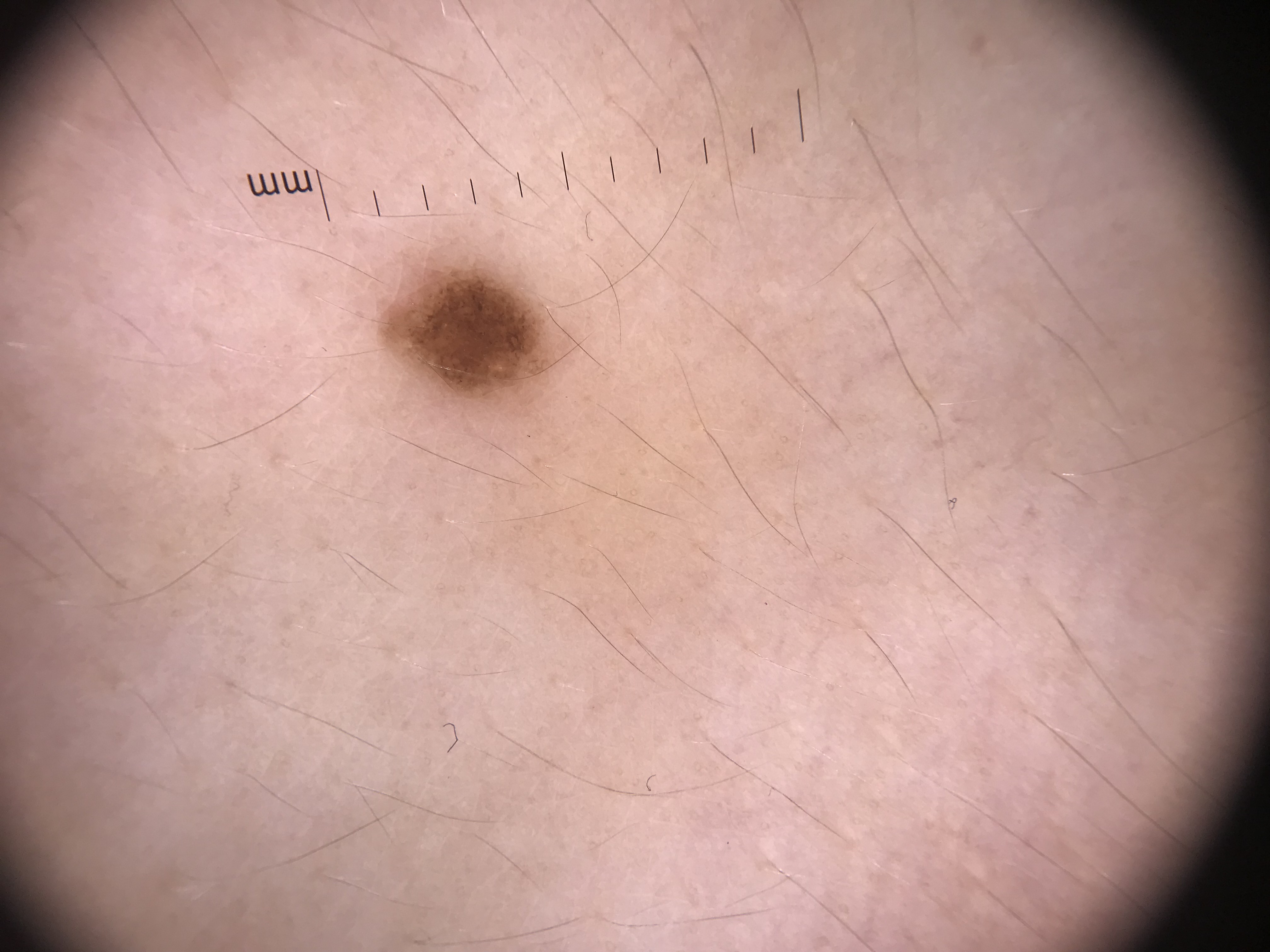Diagnosed as a junctional nevus.